A female patient age 32; history notes prior skin cancer (patient or family); the patient was assessed as FST II:
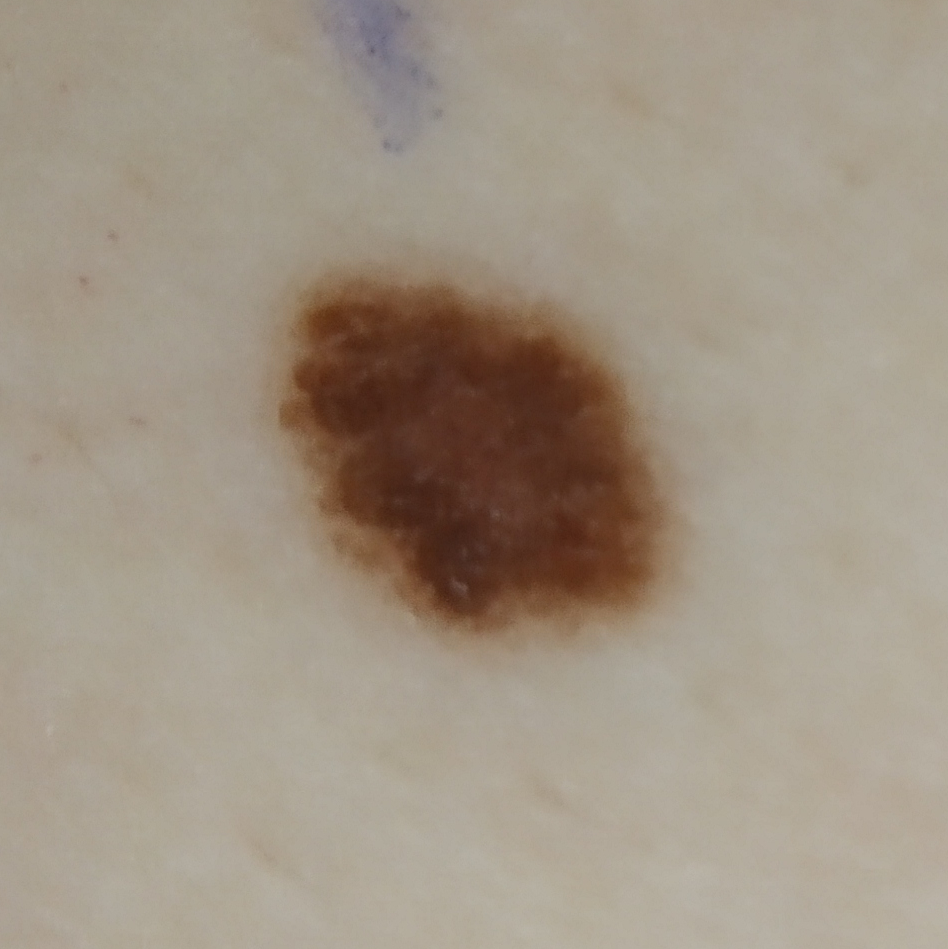  lesion_location: a thigh
  lesion_size:
    diameter_1_mm: 7.0
    diameter_2_mm: 7.0
  symptoms:
    present:
      - itching
      - change in appearance
      - growth
  diagnosis:
    name: nevus
    code: NEV
    malignancy: benign
    confirmation: histopathology